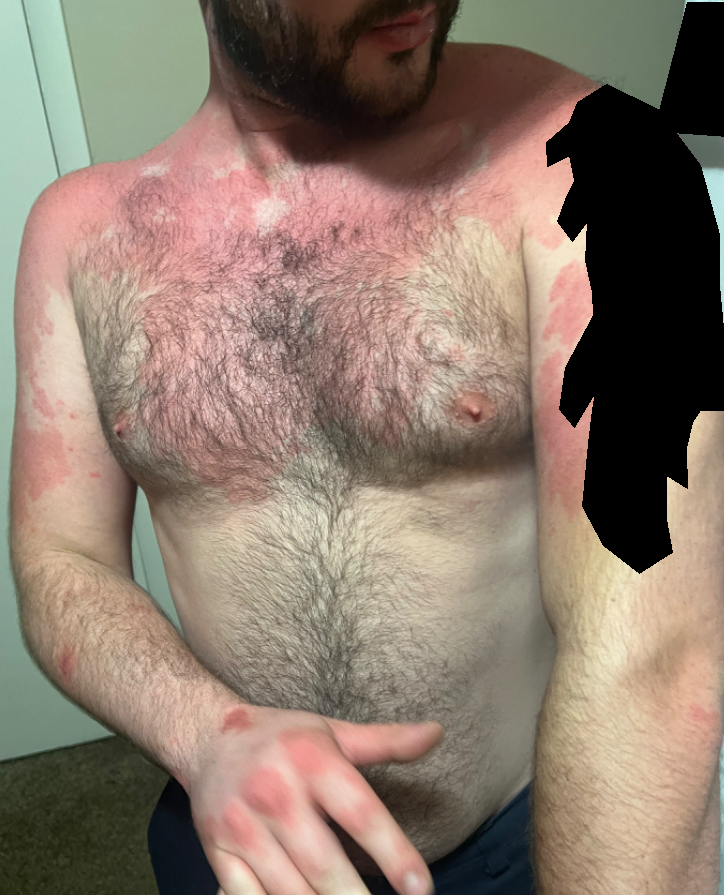patient describes the issue as: a rash; described texture: flat; framing: at an angle; subject: male, age 18–29; location: back of the hand, arm, front of the torso, back of the torso and head or neck; other reported symptoms: fatigue; skin tone: Fitzpatrick skin type II; history: more than one year; differential diagnosis: Drug Rash, Urticaria and Pityriasis rubra pilaris were considered with similar weight.